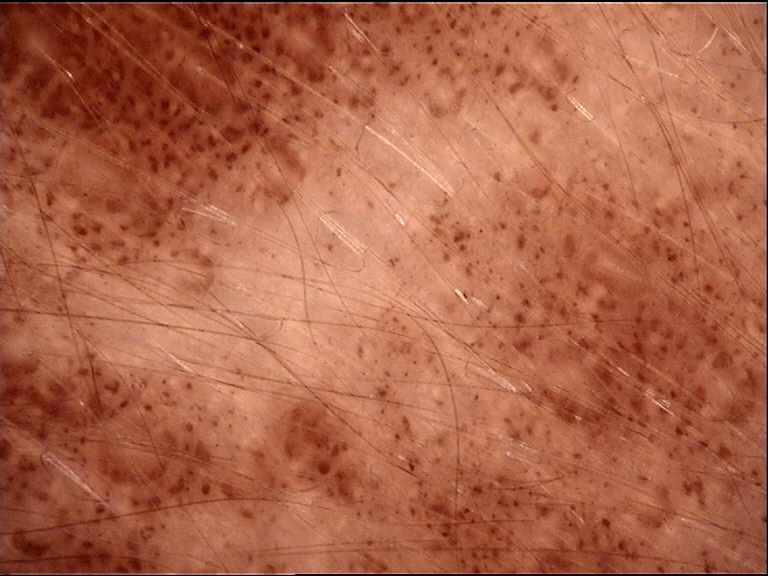{
  "diagnosis": {
    "name": "congenital junctional nevus",
    "code": "cjb",
    "malignancy": "benign",
    "super_class": "melanocytic",
    "confirmation": "expert consensus"
  }
}